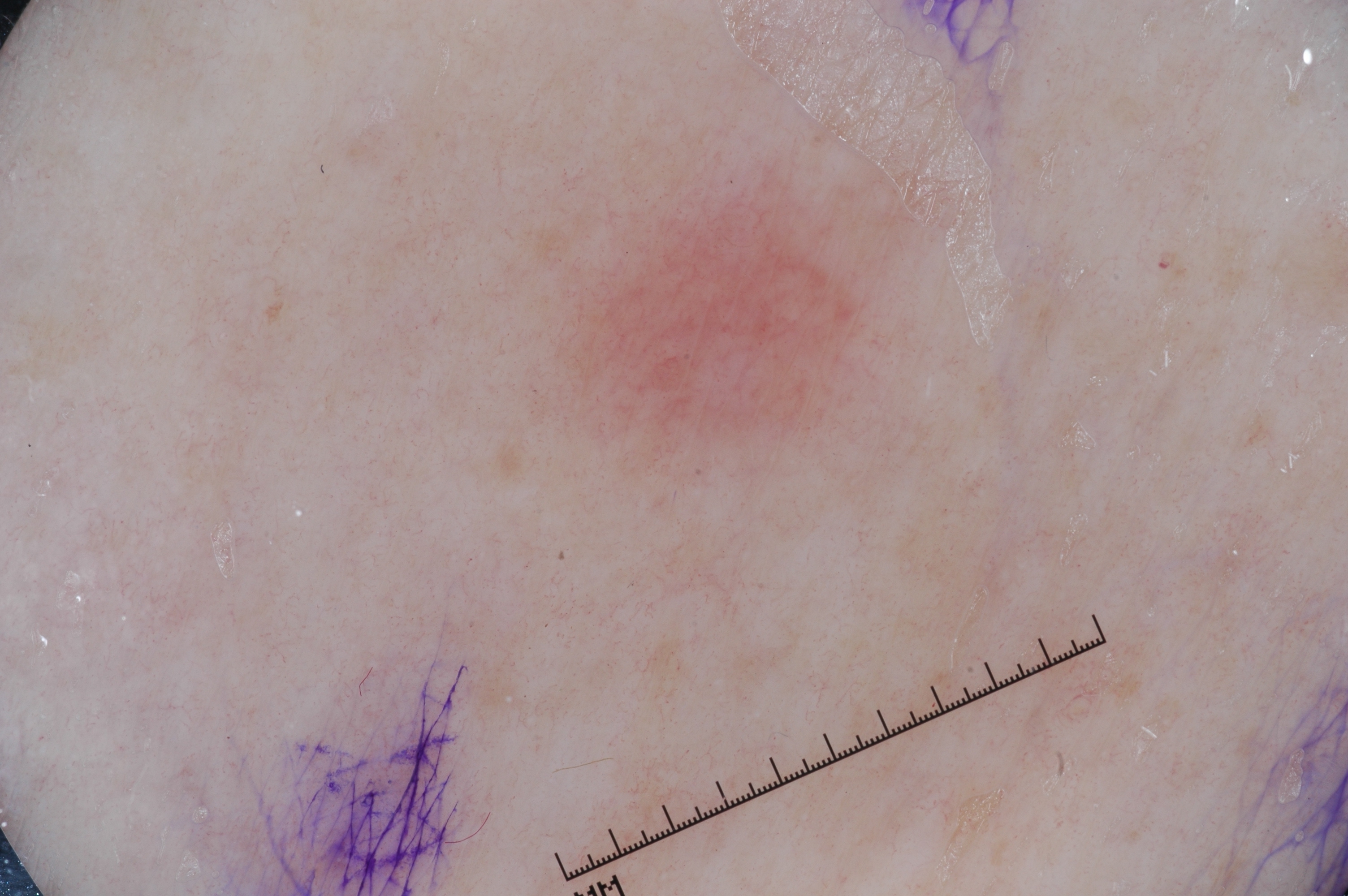{"patient": {"sex": "female", "age_approx": 75}, "image": {"modality": "dermoscopy"}, "dermoscopic_features": {"present": [], "absent": ["milia-like cysts", "streaks", "negative network", "pigment network"]}, "lesion_location": {"bbox_xyxy": [537, 147, 927, 483]}, "diagnosis": {"name": "seborrheic keratosis", "malignancy": "benign", "lineage": "keratinocytic", "provenance": "clinical"}}